The patient reported no relevant symptoms from the lesion. The patient described the issue as a rash. The contributor is a male aged 50–59. The affected area is the arm. An image taken at a distance:
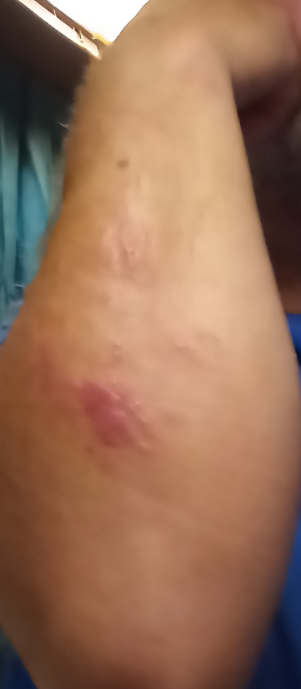On independent review by the dermatologists, consistent with Contact dermatitis.